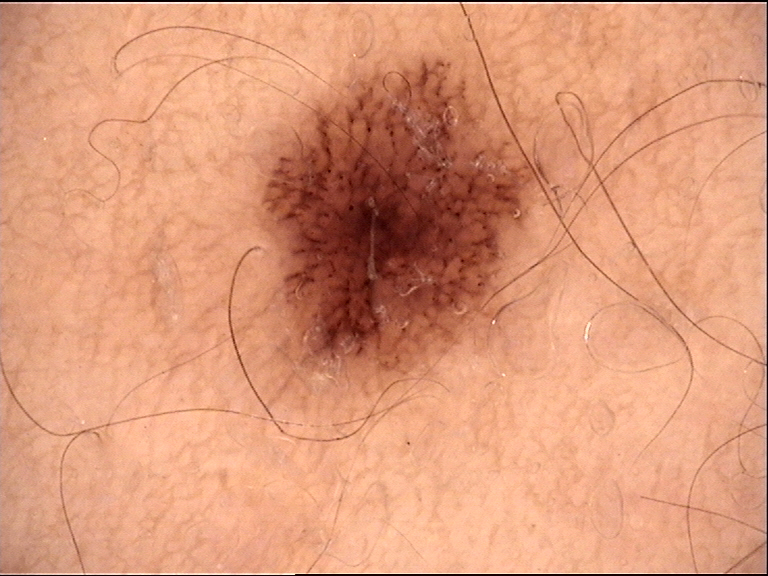A dermoscopic image of a skin lesion.
Diagnosed as a dysplastic junctional nevus.